A dermoscopy image of a single skin lesion: 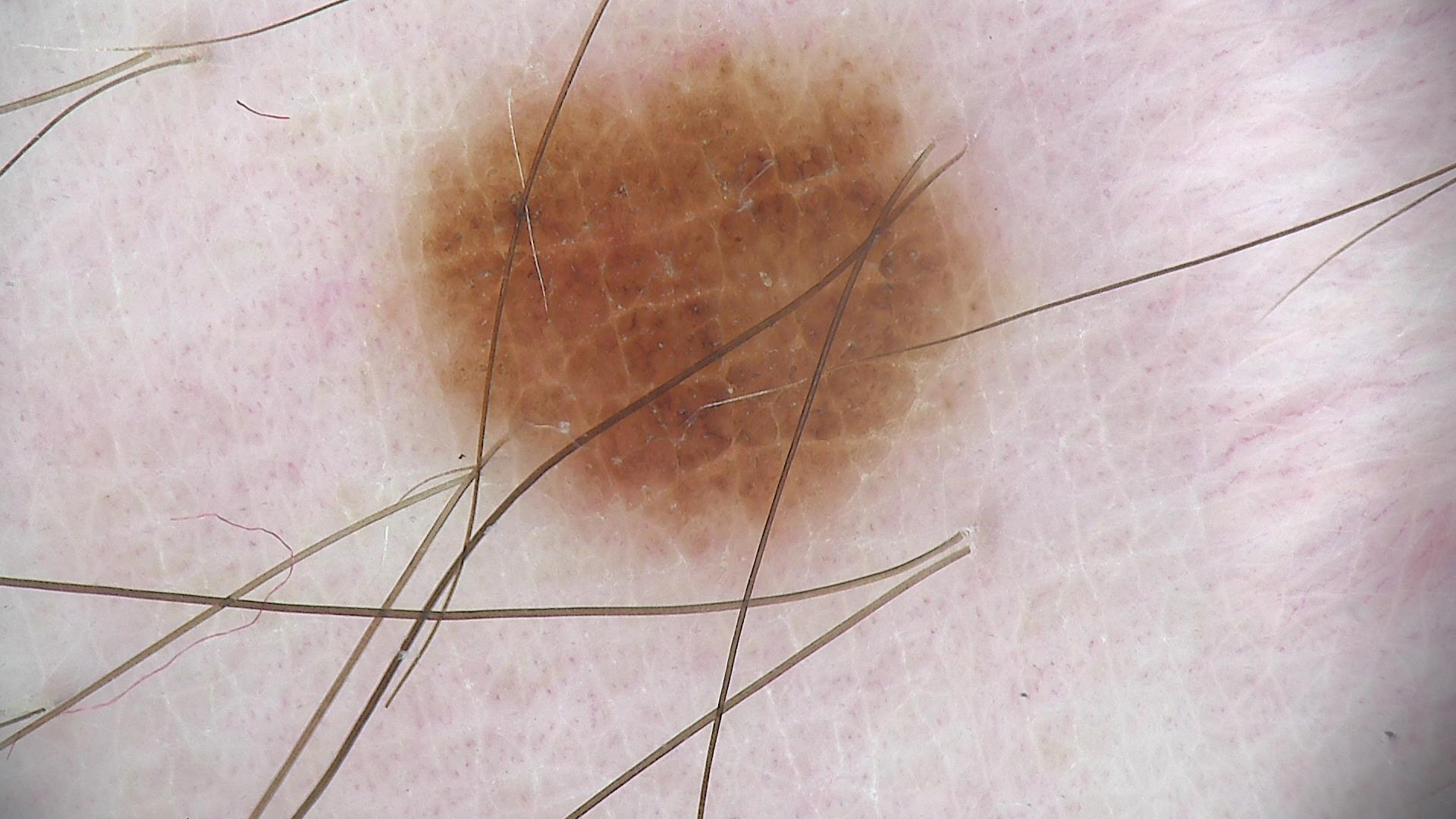Labeled as a dysplastic junctional nevus.